The patient says their skin reddens with sun exposure. A clinical photograph of a skin lesion. Imaged for a research study, with no referral diagnosis recorded. A male patient aged 62: 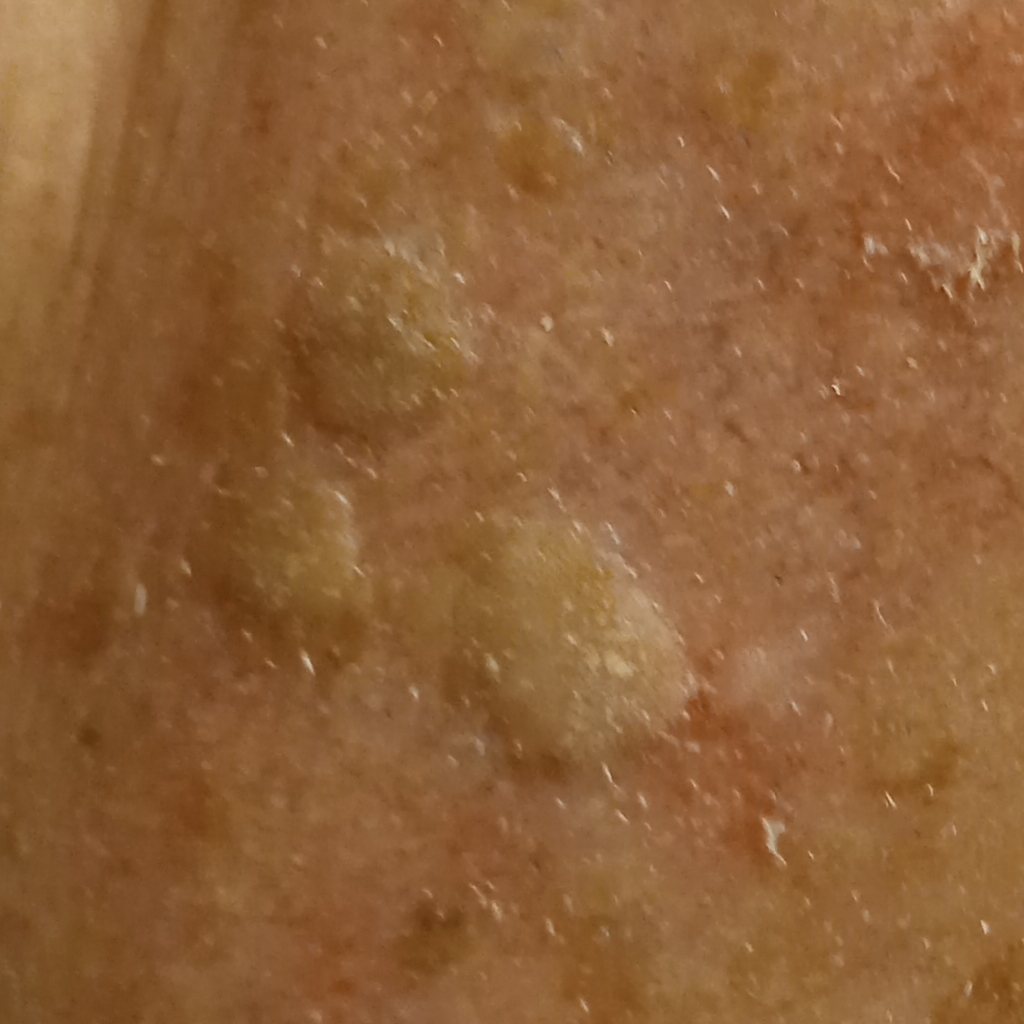– location — the face
– assessment — seborrheic keratosis (dermatologist consensus)